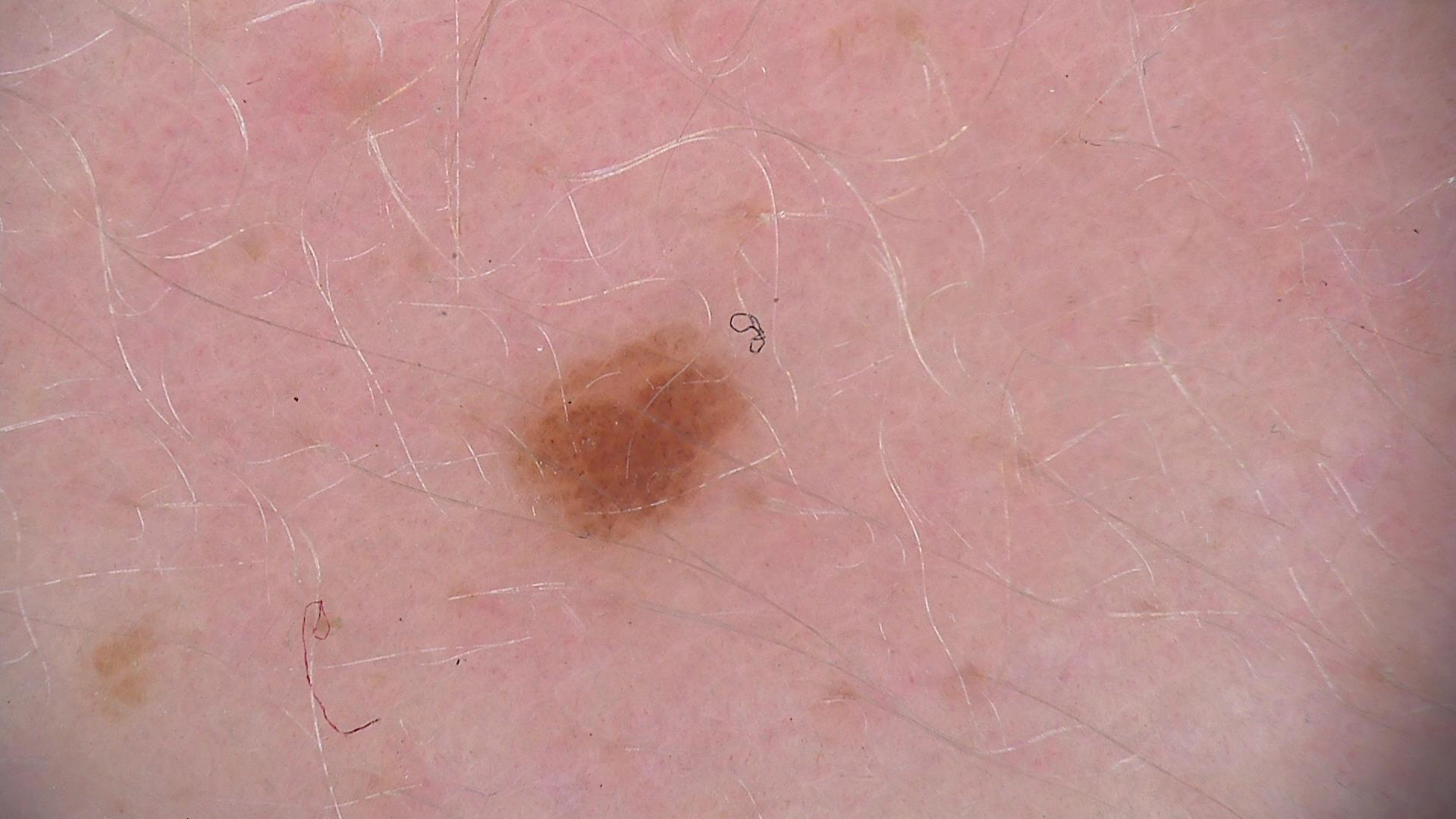assessment: dysplastic junctional nevus (expert consensus)